A dermoscopic view of a skin lesion: 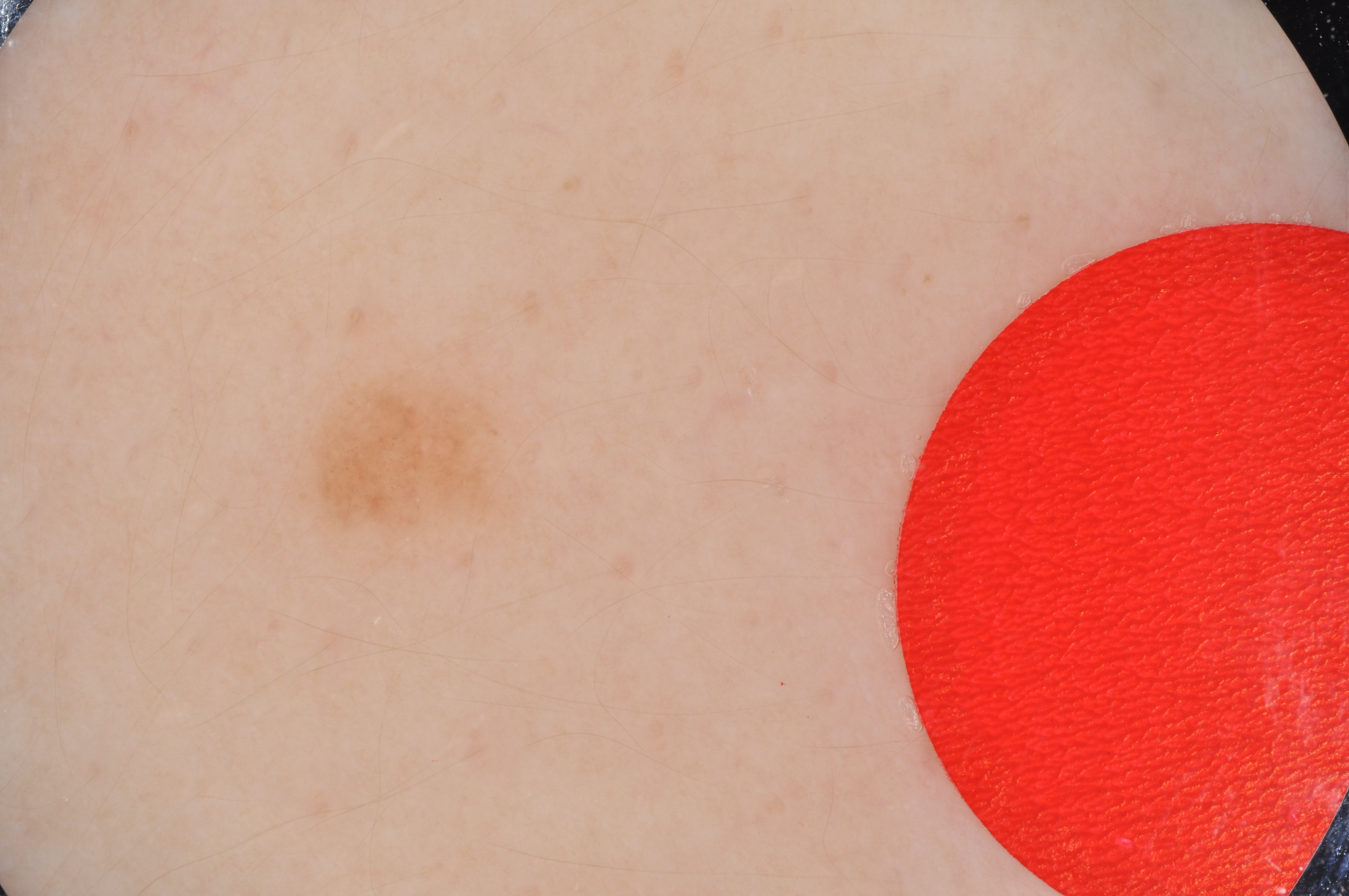| feature | finding |
|---|---|
| lesion location | [292, 360, 557, 555] |
| impression | a benign lesion |